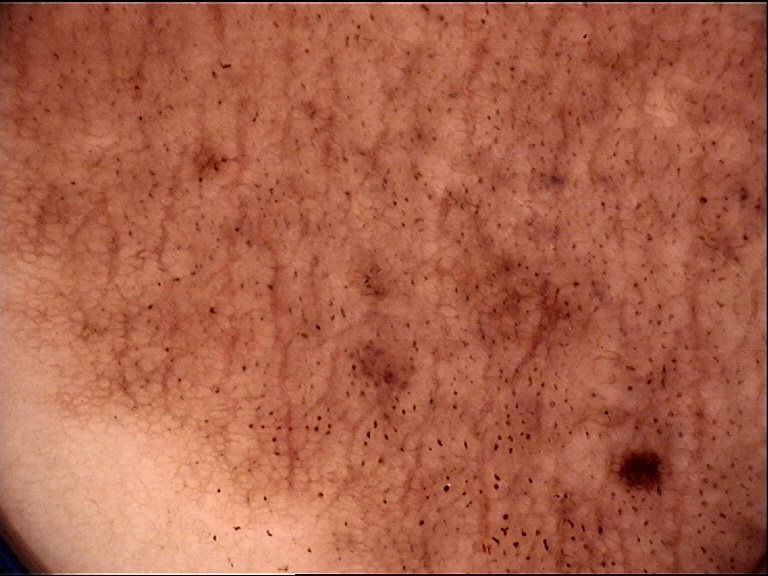Dermoscopy of a skin lesion.
The diagnostic label was a banal lesion — a congenital junctional nevus.